Reported duration is less than one week; the lesion is associated with itching; texture is reported as raised or bumpy; this image was taken at a distance; the arm is involved; the patient considered this a rash.
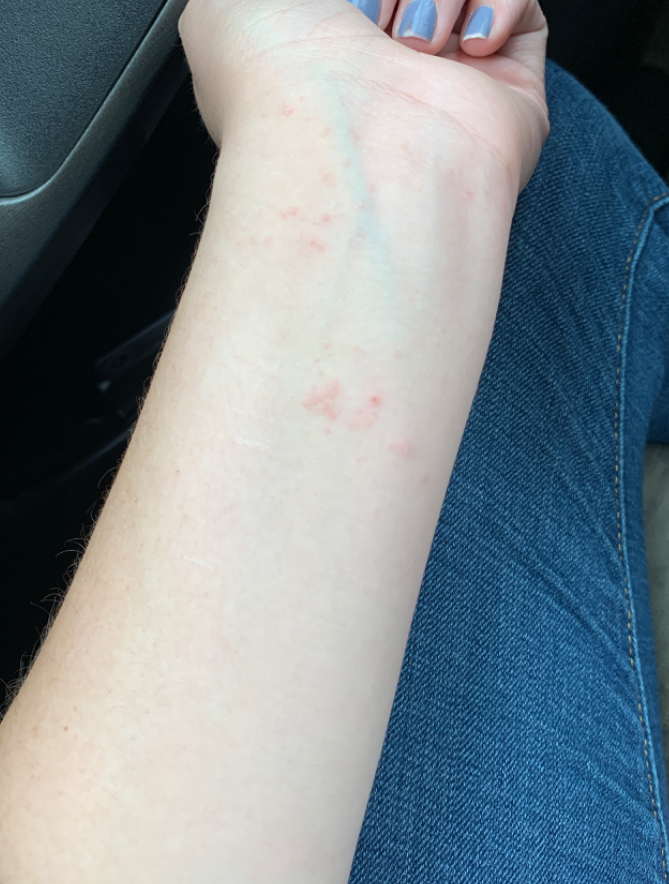Assessment: A single dermatologist reviewed the case: the leading consideration is Allergic Contact Dermatitis; possibly Lichen planus/lichenoid eruption; also raised was Eczema.